Dermoscopy of a skin lesion: 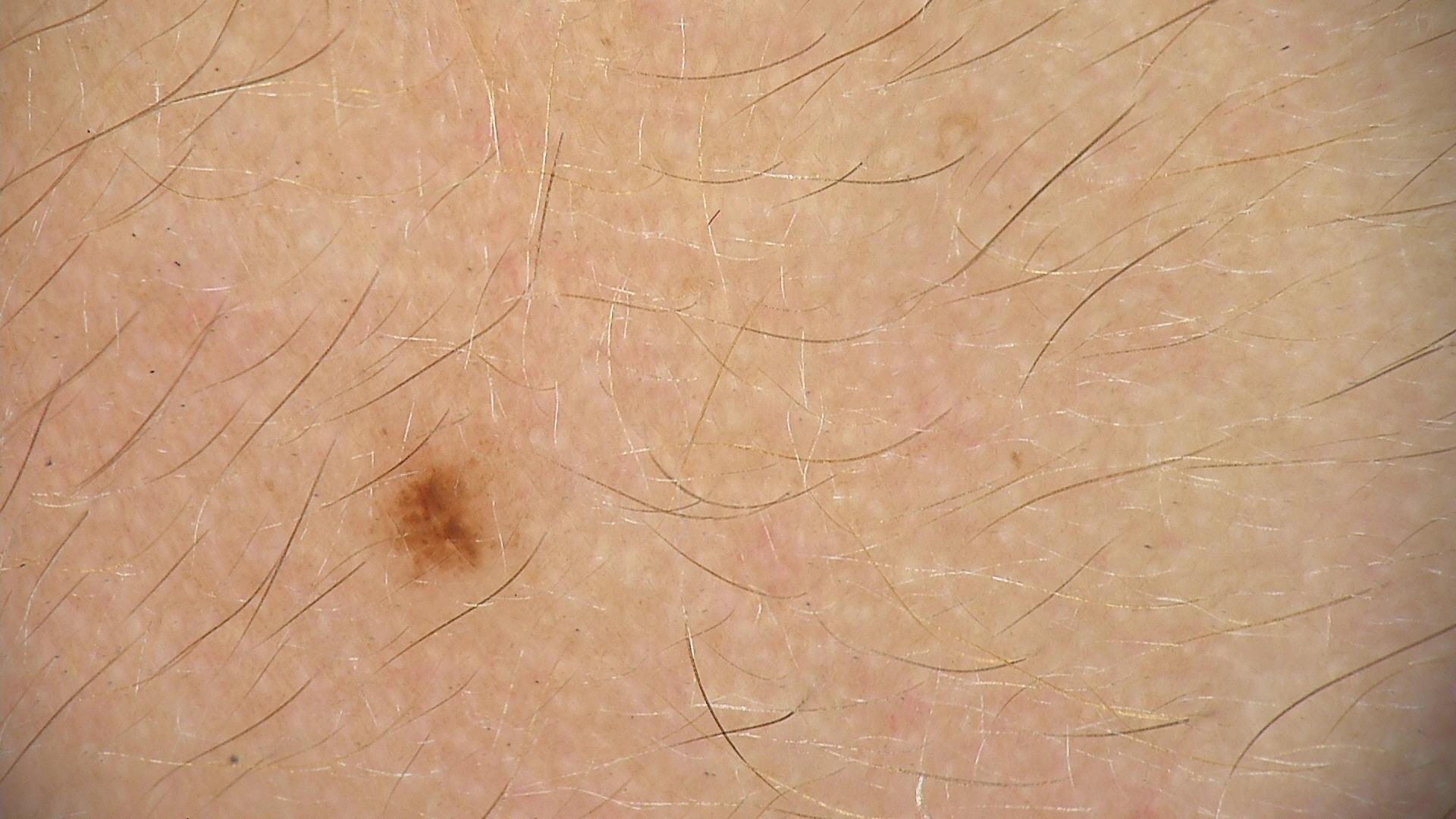diagnostic label: dysplastic junctional nevus (expert consensus).